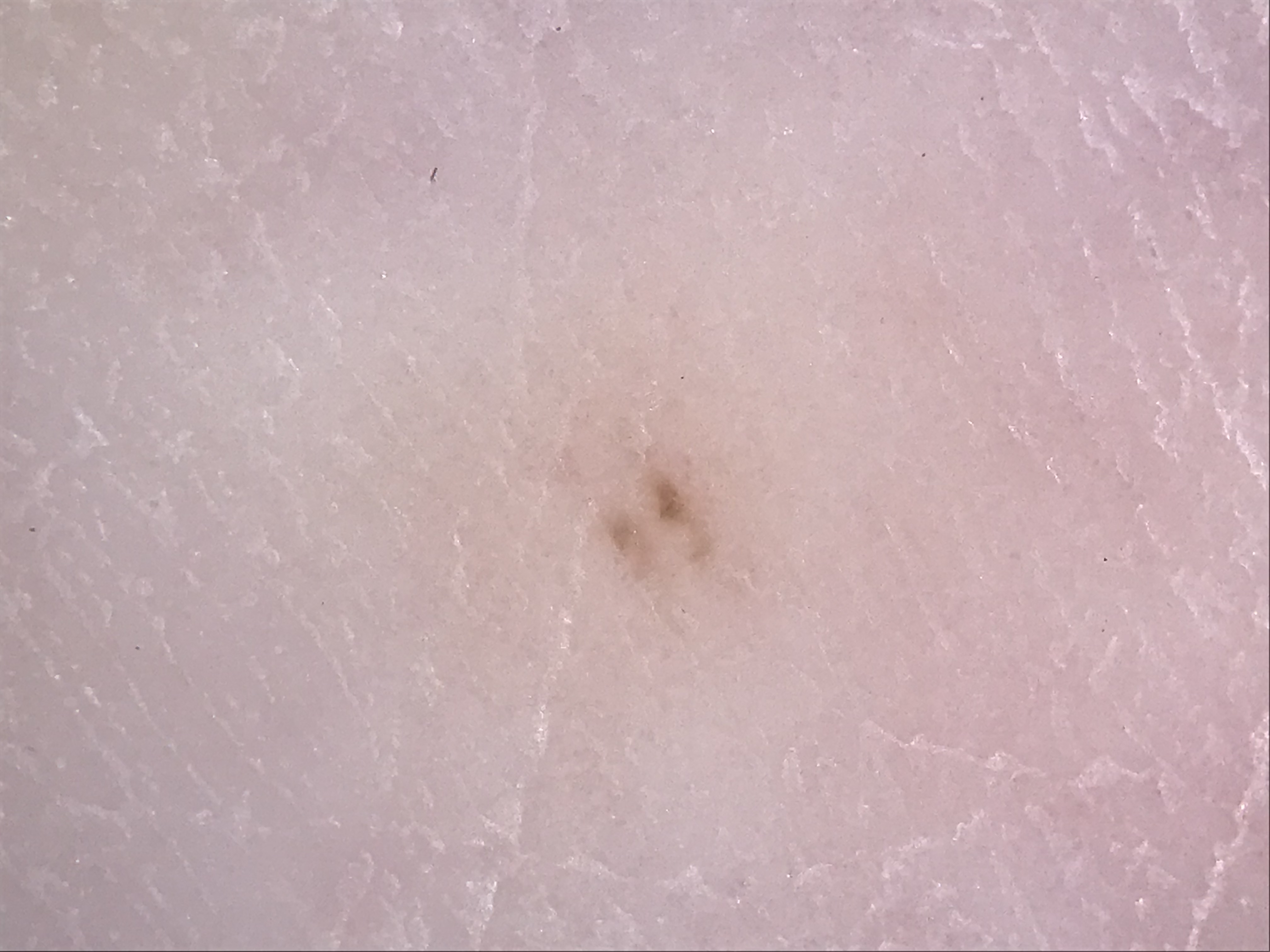Case:
A dermoscopic close-up of a skin lesion. The architecture is that of a banal lesion.
Conclusion:
Consistent with an acral junctional nevus.